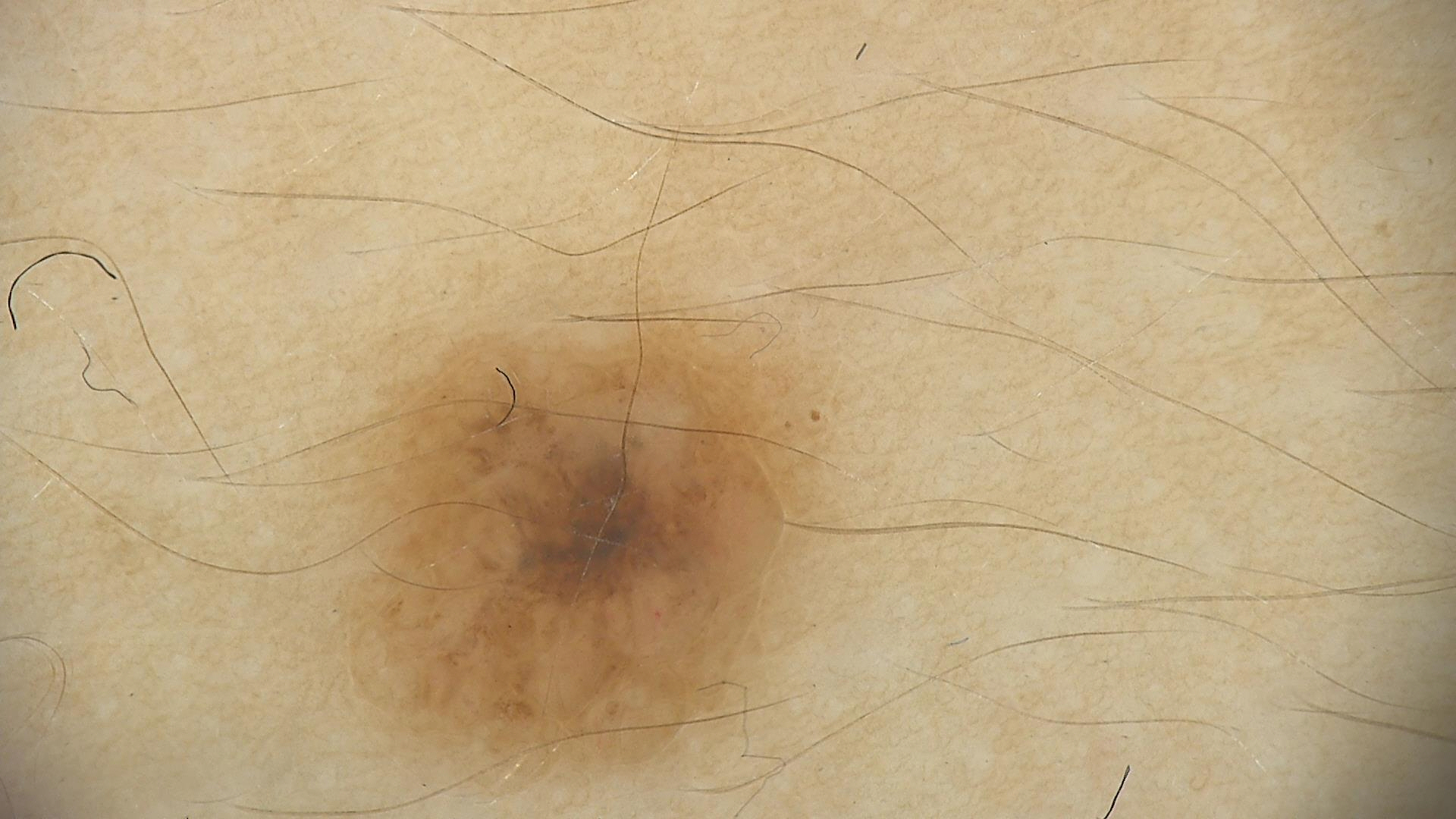label=dermal nevus (expert consensus)